Texture is reported as rough or flaky, raised or bumpy and fluid-filled · an image taken at a distance · the patient also reports joint pain and fatigue · symptoms reported: pain, darkening, bleeding, enlargement, itching, bothersome appearance and burning · the condition has been present for three to twelve months · located on the leg.
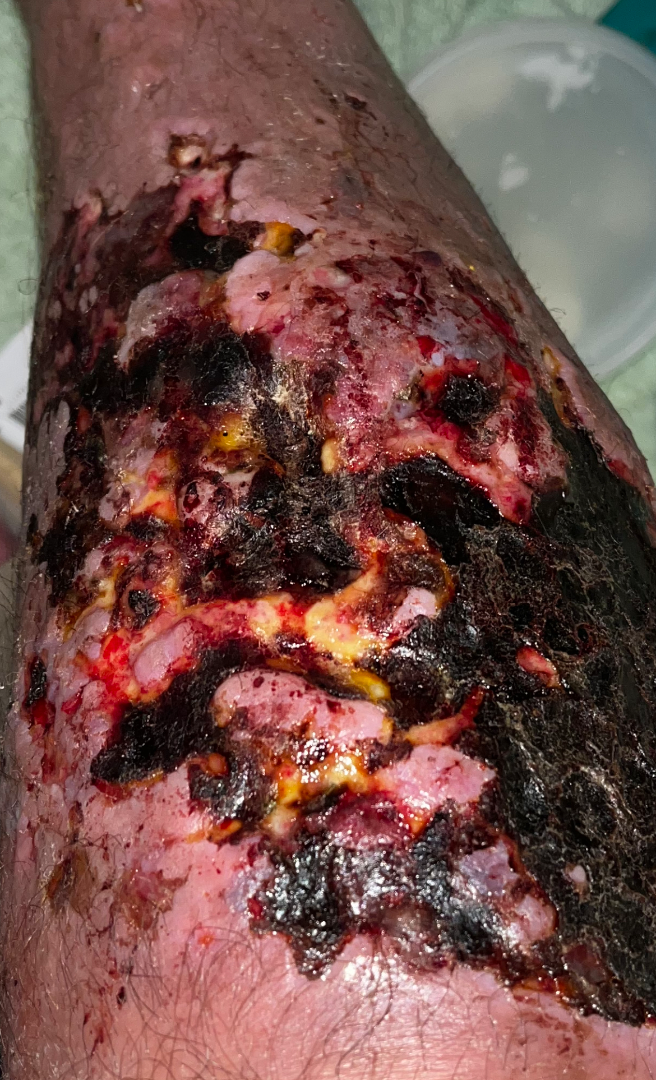Review: The skin condition could not be confidently assessed from this image.